A subject in their 60s — 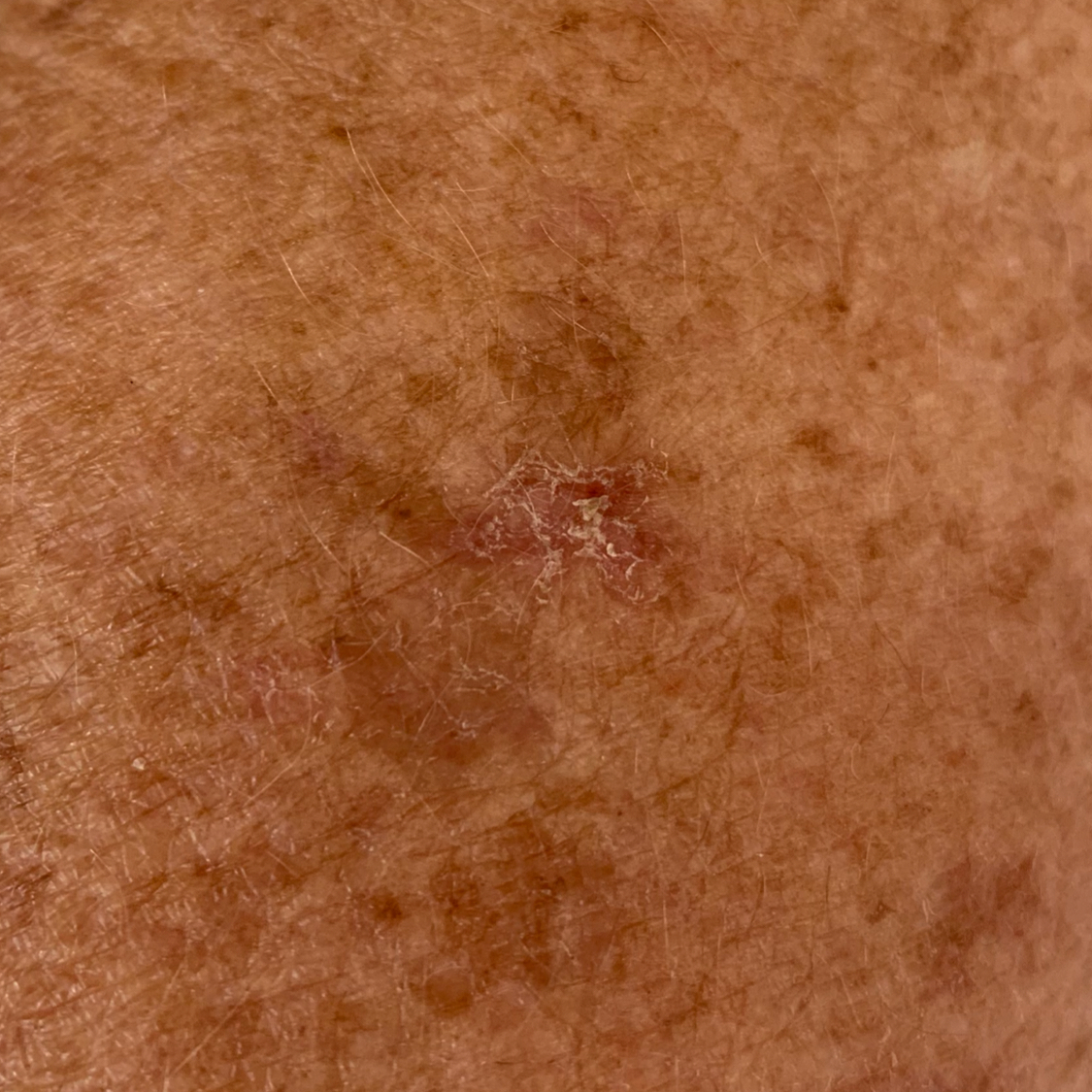The lesion is located on a forearm. No symptoms reported. The clinical impression was an actinic keratosis.